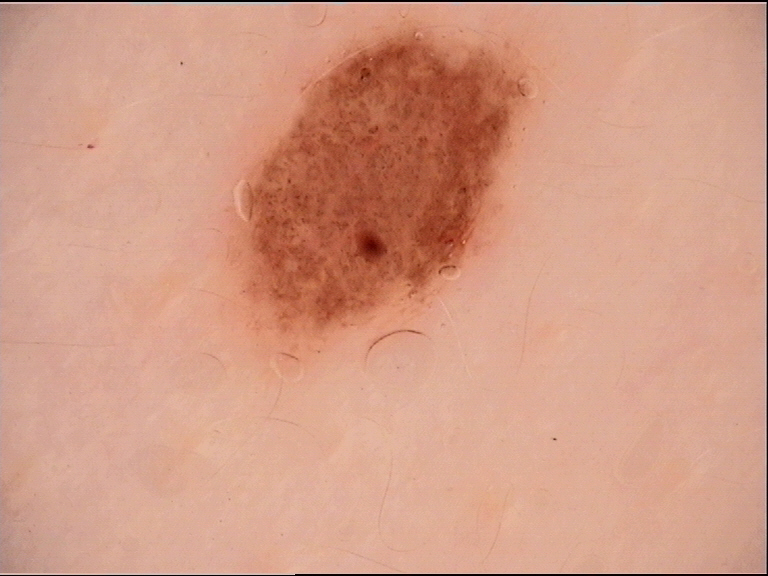imaging: dermatoscopy; diagnostic label: dysplastic junctional nevus (expert consensus).